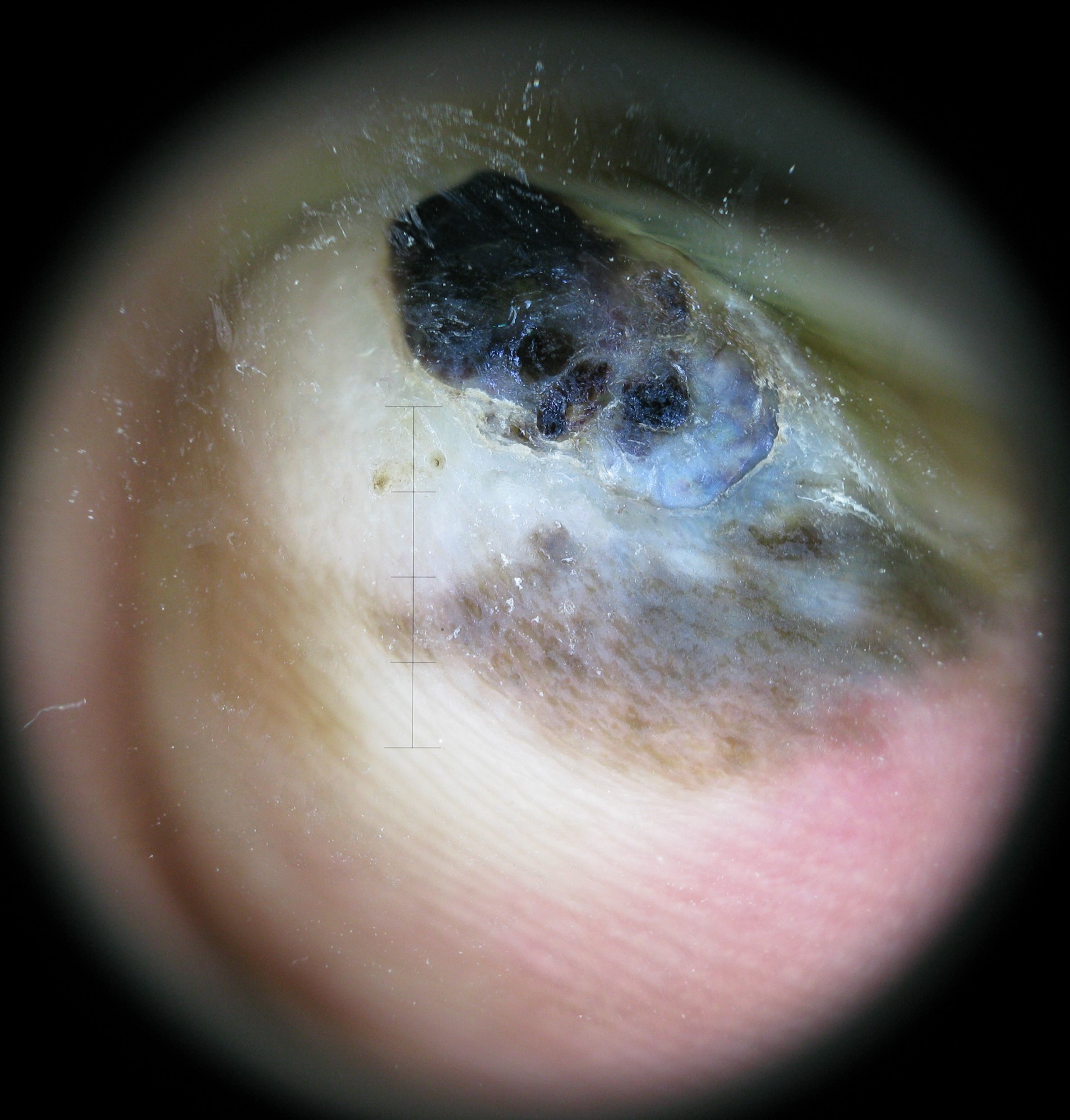Findings:
• imaging — dermatoscopy
• class — acral nodular melanoma (biopsy-proven)